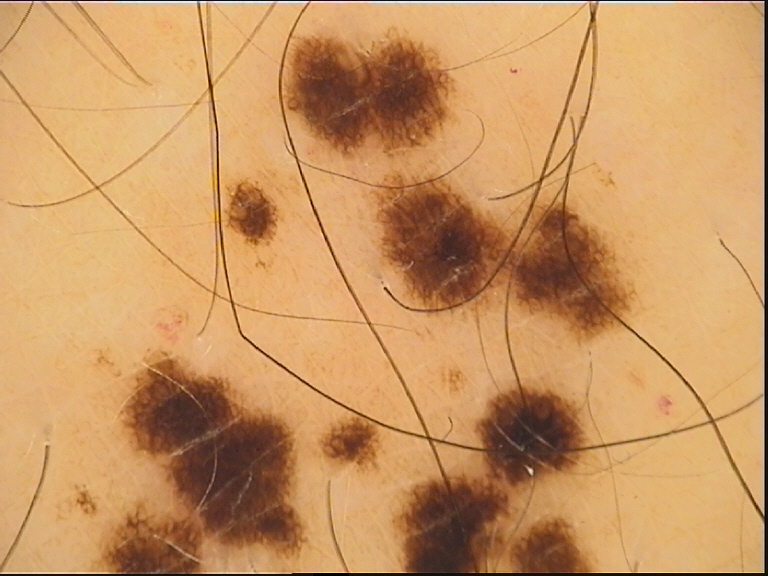Consistent with a benign lesion — a dysplastic junctional nevus.